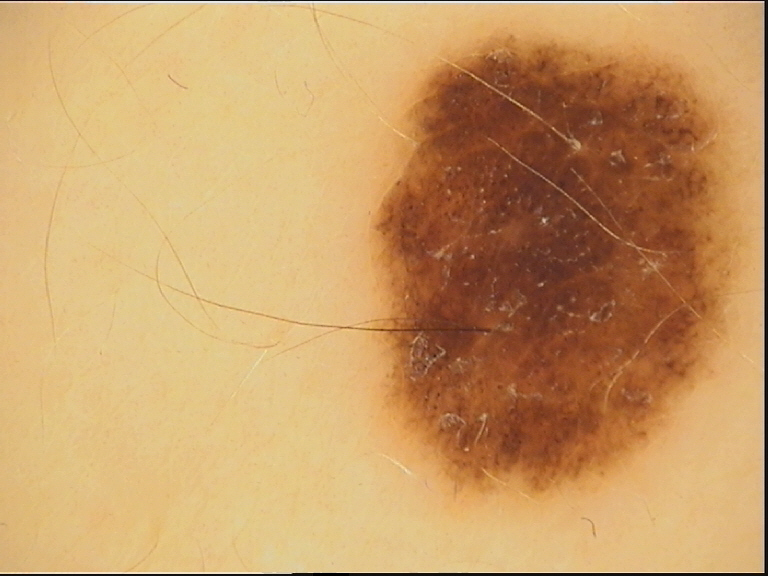Consistent with a benign lesion — a dysplastic compound nevus.